A macroscopic clinical photograph of a skin lesion · the patient says their skin reddens painfully with sun exposure · acquired for a research image collection, with no referral diagnosis · a male patient 65 years of age · the patient describes having numerous moles:
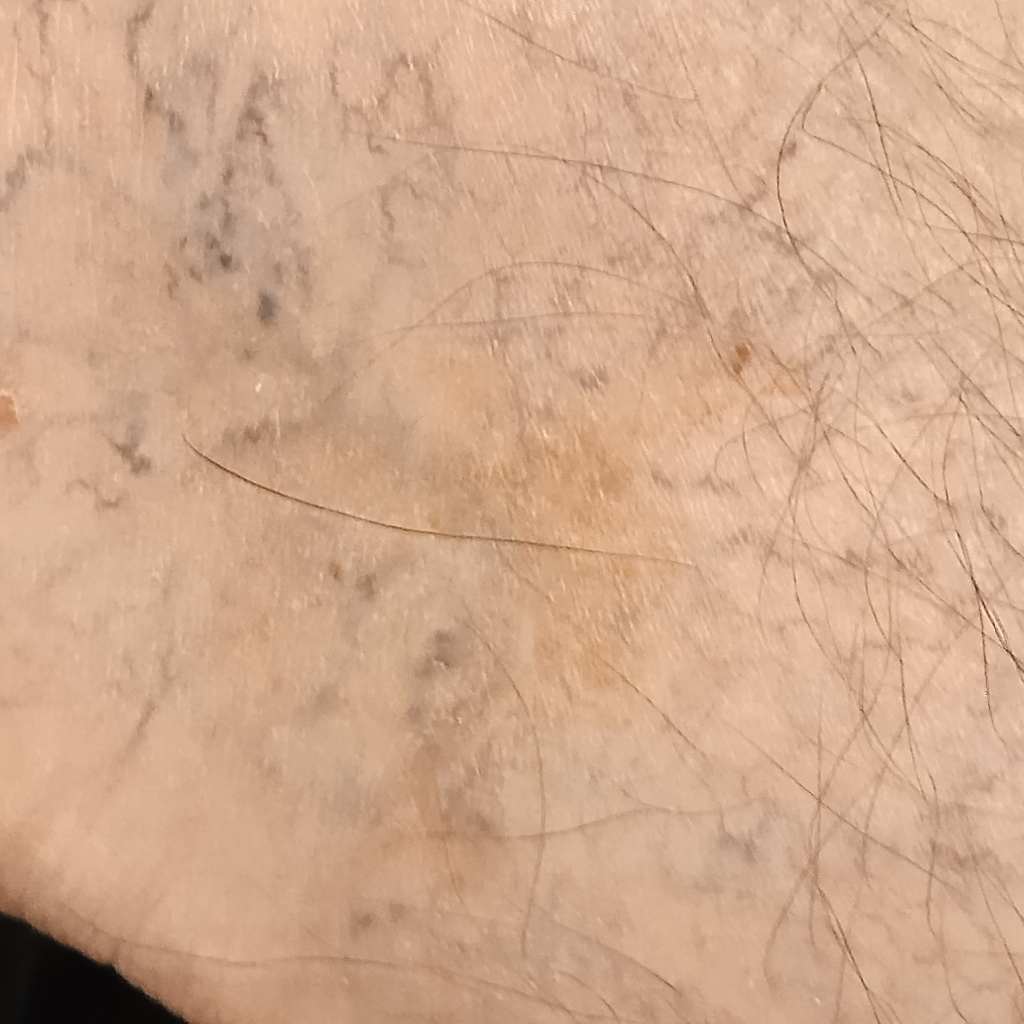Located on a leg.
The lesion is about 13 mm across.
The diagnostic impression was a basal cell carcinoma.